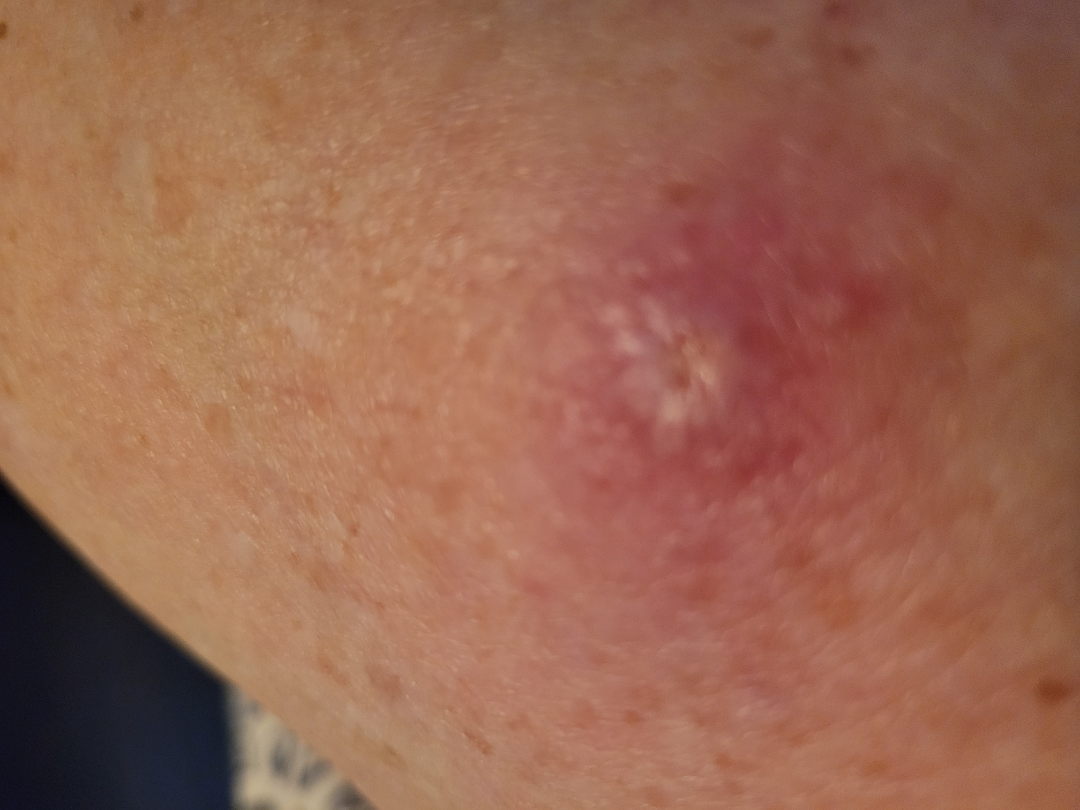The patient notes the lesion is raised or bumpy and fluid-filled. Present for less than one week. The photograph is a close-up of the affected area. The leg is involved. Skin tone: Fitzpatrick III. Reported lesion symptoms include enlargement, bothersome appearance, darkening, bleeding and pain. The patient is 70–79, female. The reviewing dermatologist's impression was: Abscess and Insect Bite were considered with similar weight; lower on the differential is SCC/SCCIS.